An image taken at a distance · reported duration is more than five years · the leg is involved · skin tone: Fitzpatrick phototype V · the patient described the issue as a growth or mole · the patient is female: 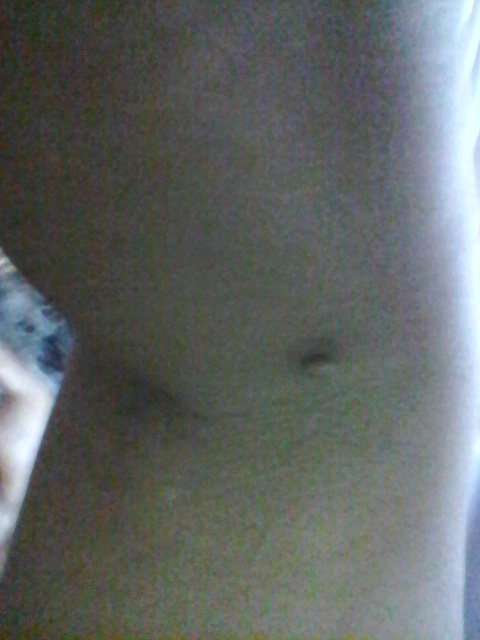Findings: The skin findings could not be characterized from the image.